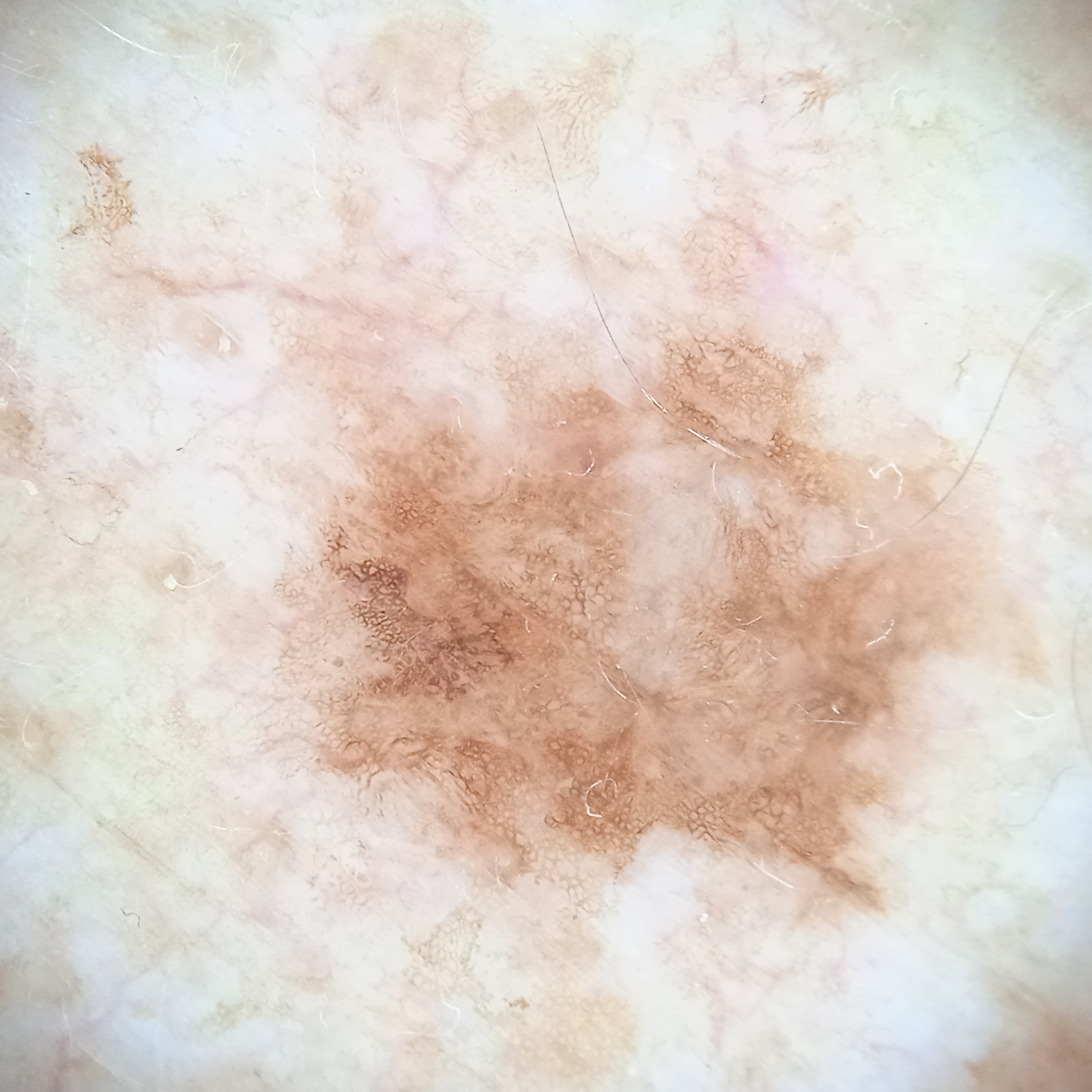The lesion was left diagnostically undetermined on review. Summary: A male patient 81 years old. Dermoscopy of a skin lesion. Collected as part of a research study, without a referral diagnosis. The lesion is located on the back. The lesion measures approximately 8 mm.